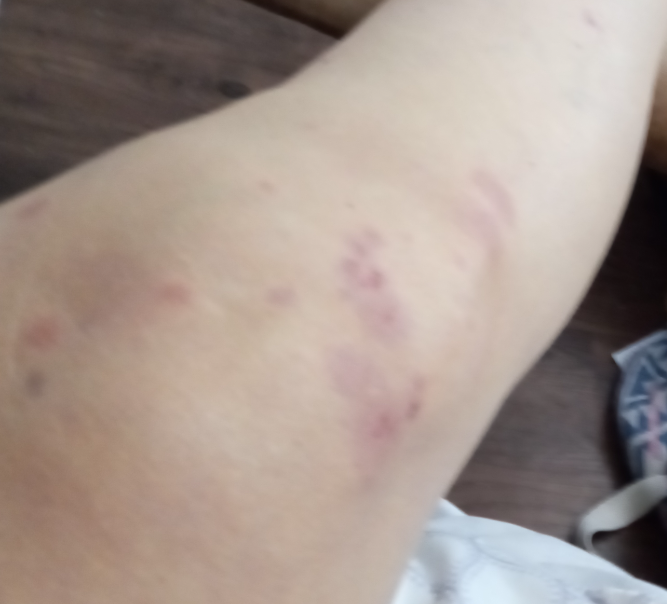Assessment: The skin findings could not be characterized from the image. Clinical context: The front of the torso, top or side of the foot and leg are involved. The photograph was taken at a distance. Texture is reported as raised or bumpy. The contributor is 60–69, female. Symptoms reported: pain, enlargement and itching. FST II.